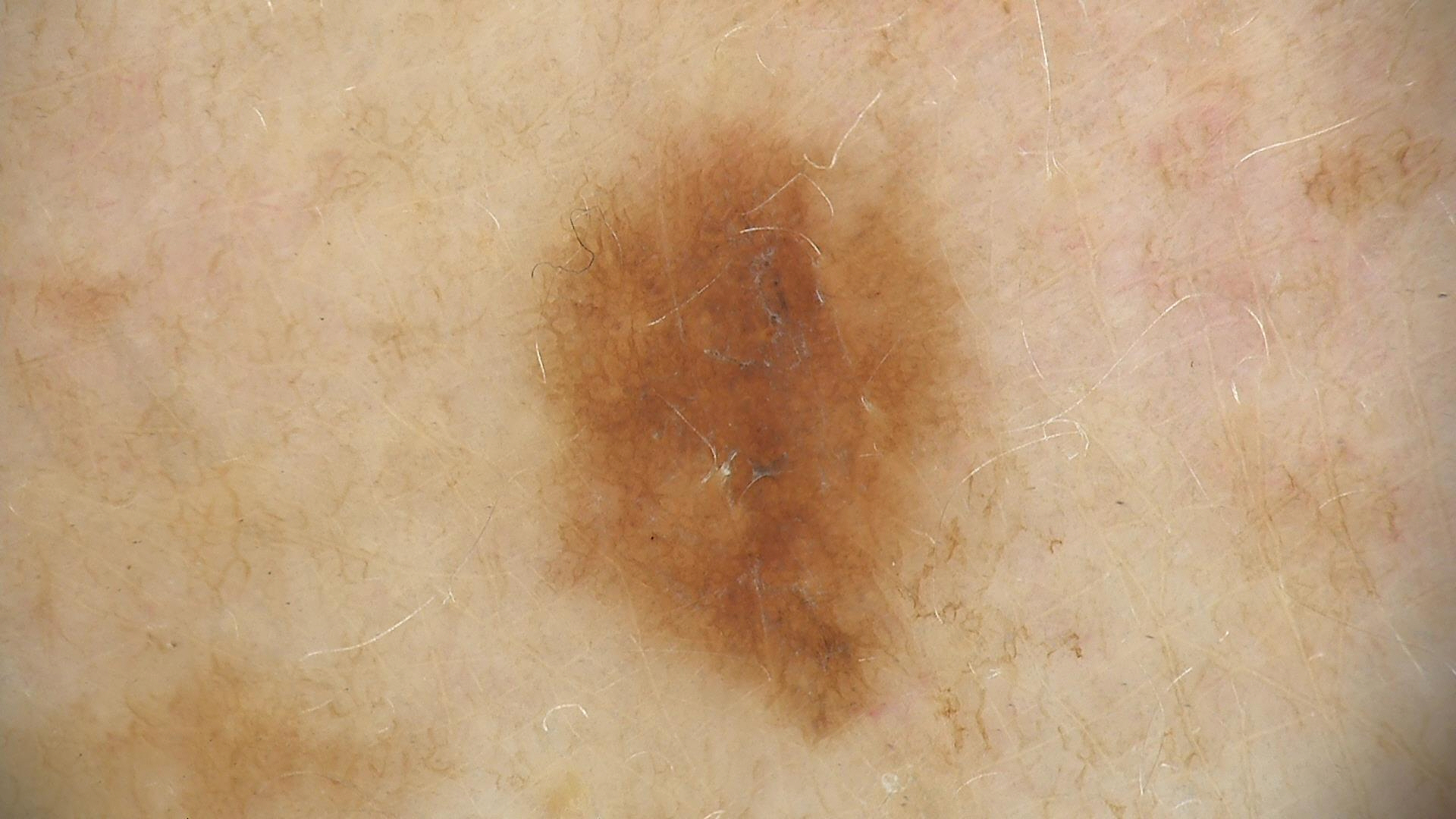image=dermatoscopy; assessment=dysplastic junctional nevus (expert consensus).